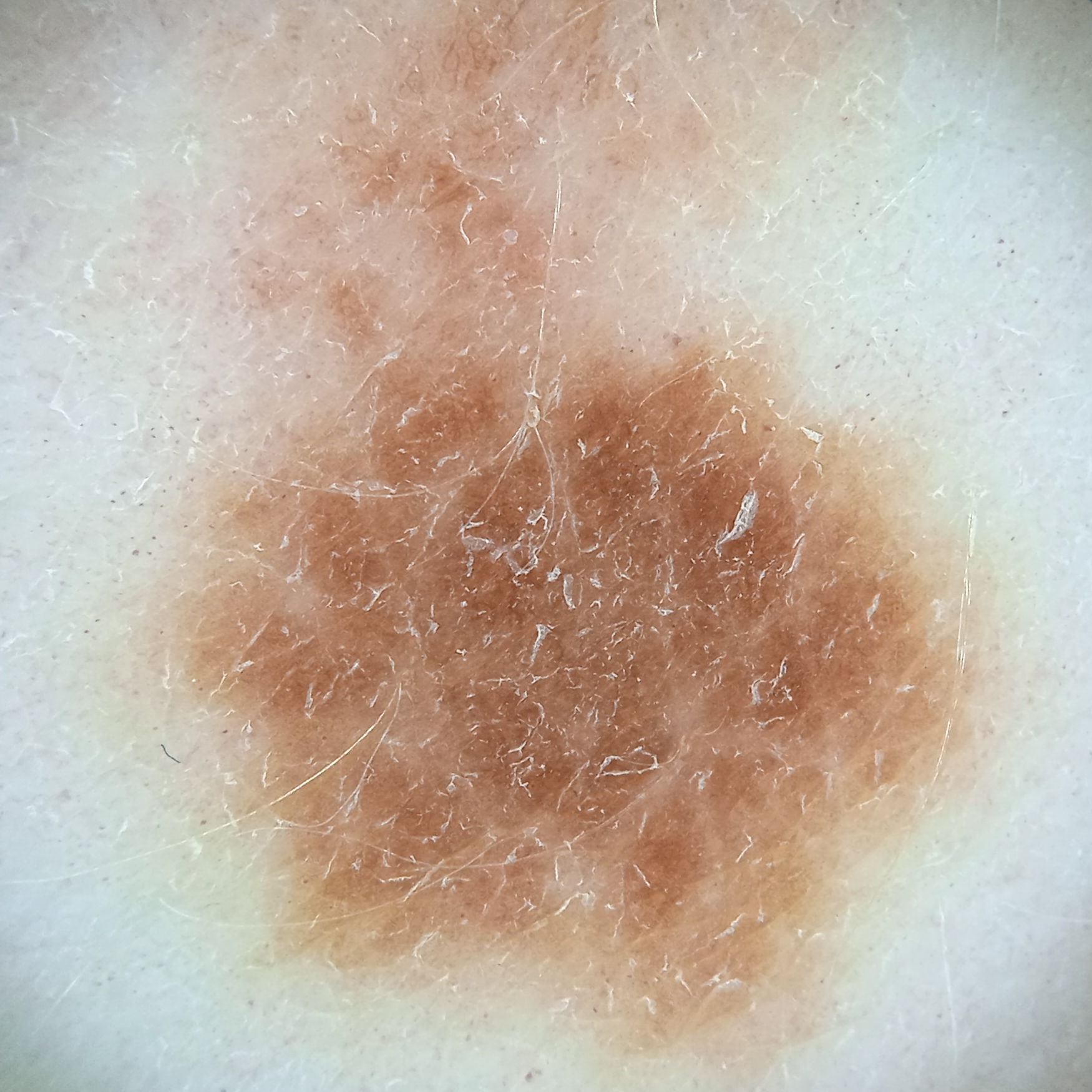Clinical context: Dermoscopy of a skin lesion. A female patient 54 years old. Numerous moles by the patient's own estimate. On a questionnaire the patient reported a personal history of cancer, a family history of skin cancer, and a personal history of skin cancer. The lesion is about 17.5 mm across. Conclusion: The diagnostic impression was a melanoma.